Acquired for a research image collection, with no referral diagnosis; a female patient 48 years of age: 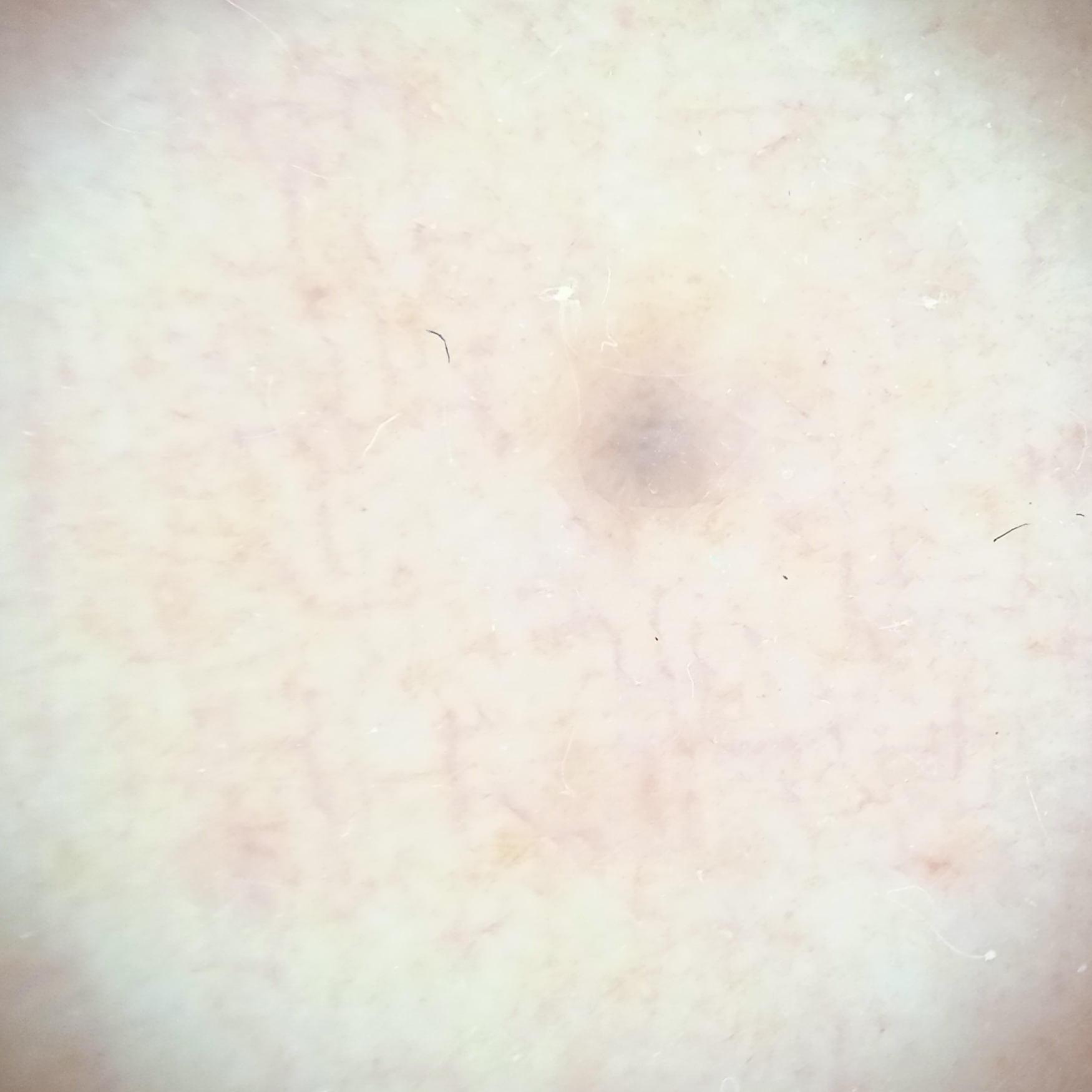Summary:
Located on an arm. Measuring roughly 1.8 mm.
Assessment:
Dermatologist review favored a melanocytic nevus.